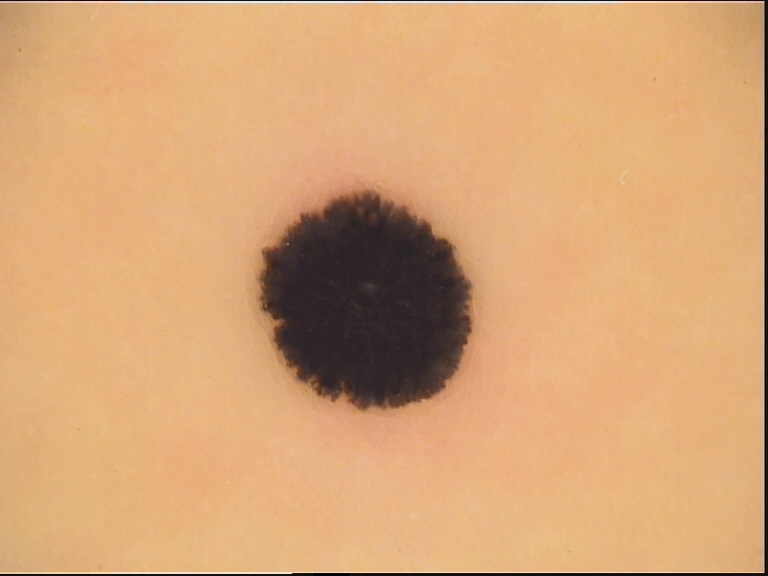imaging: dermatoscopy | diagnostic label: Spitz/Reed nevus (expert consensus).